An image taken at a distance: 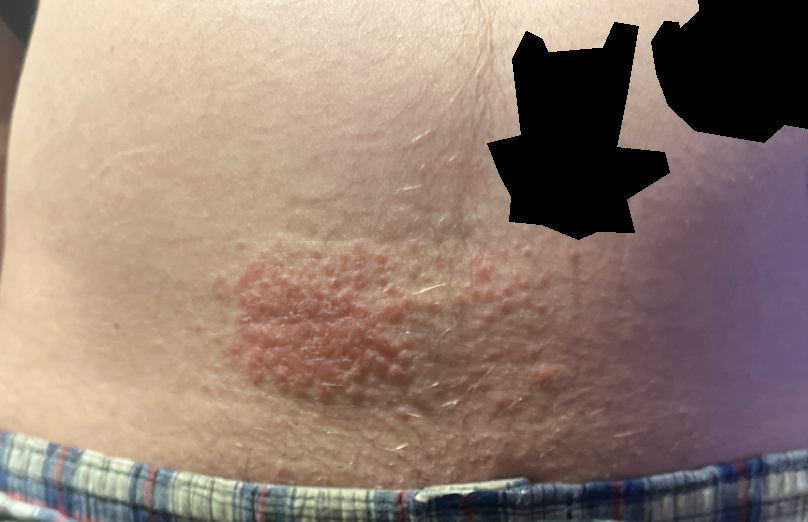assessment — indeterminate from the photograph.